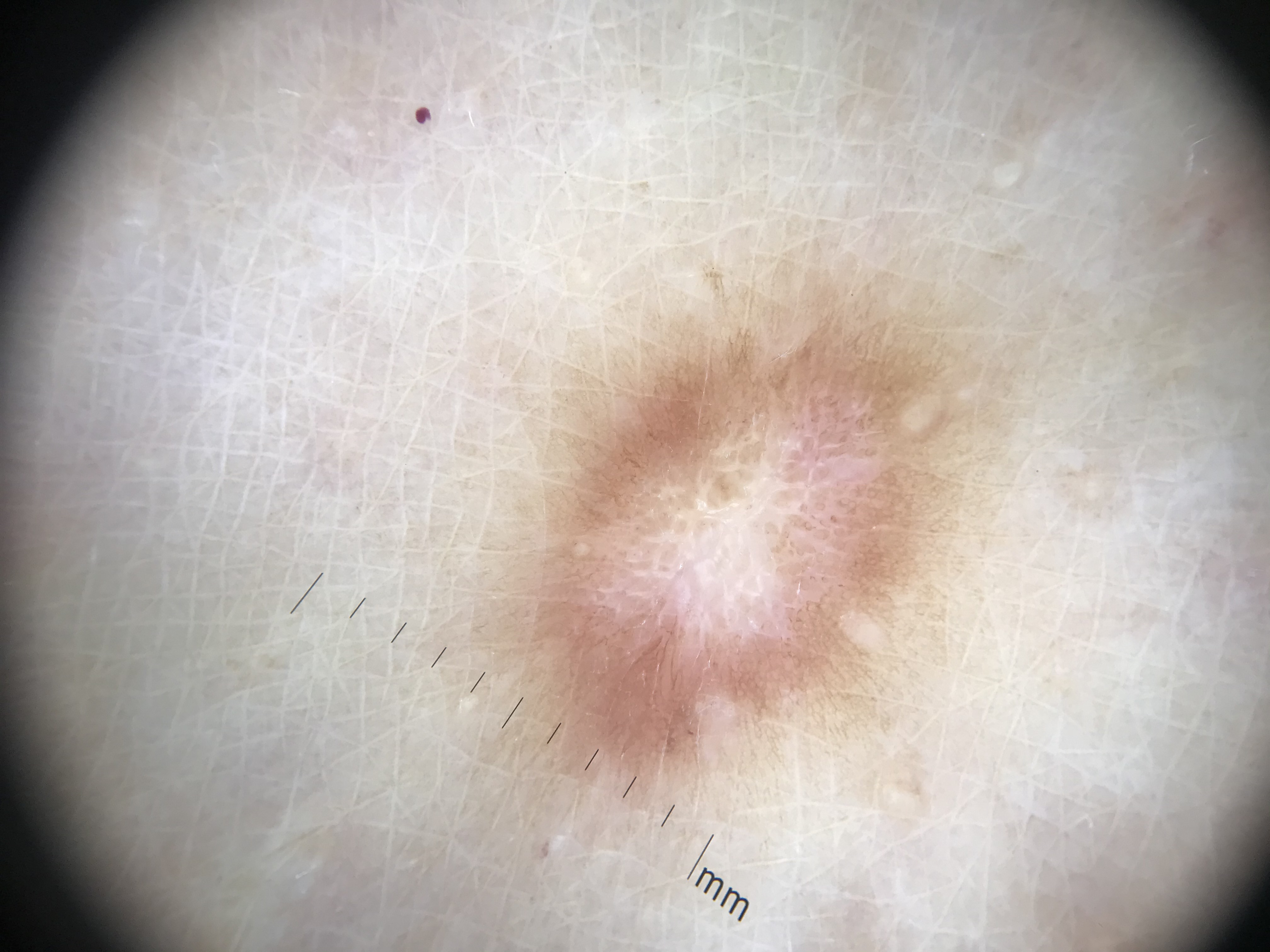Conclusion:
Consistent with a dermatofibroma.